Close-up view. The patient reports the lesion is raised or bumpy. The contributor is 30–39, female. The patient reports bothersome appearance. The head or neck is involved. The patient reports the condition has been present for three to twelve months. No relevant systemic symptoms:
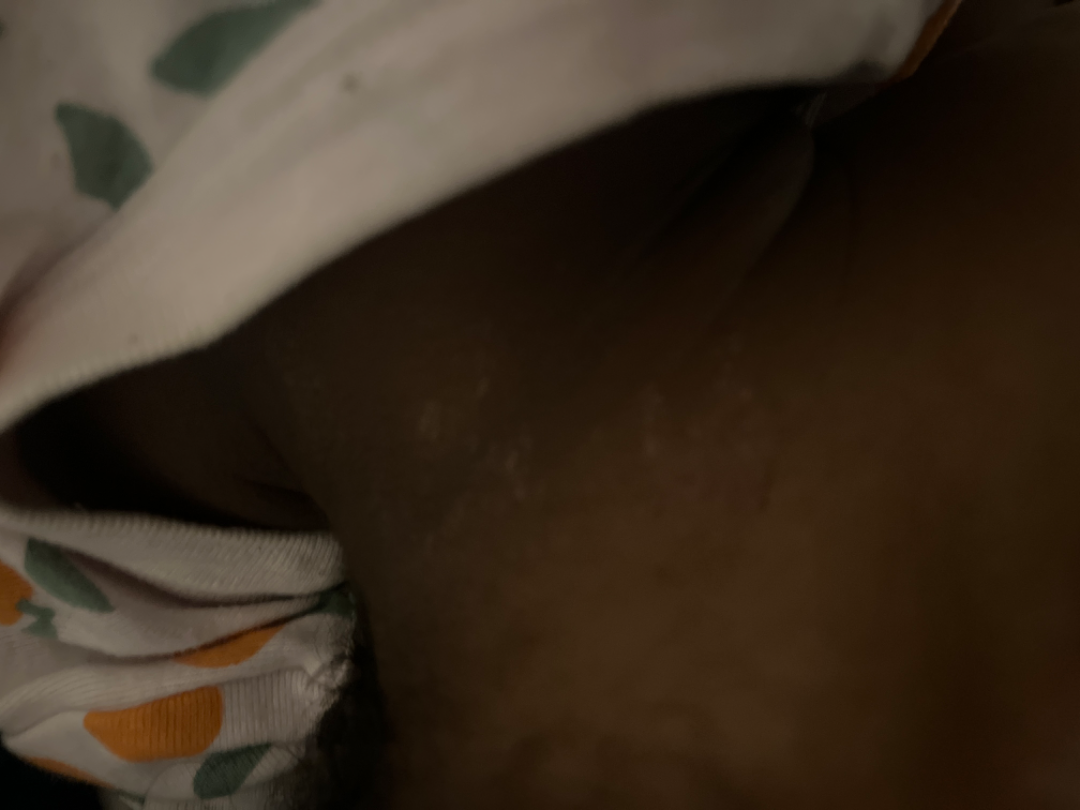assessment — unable to determine.